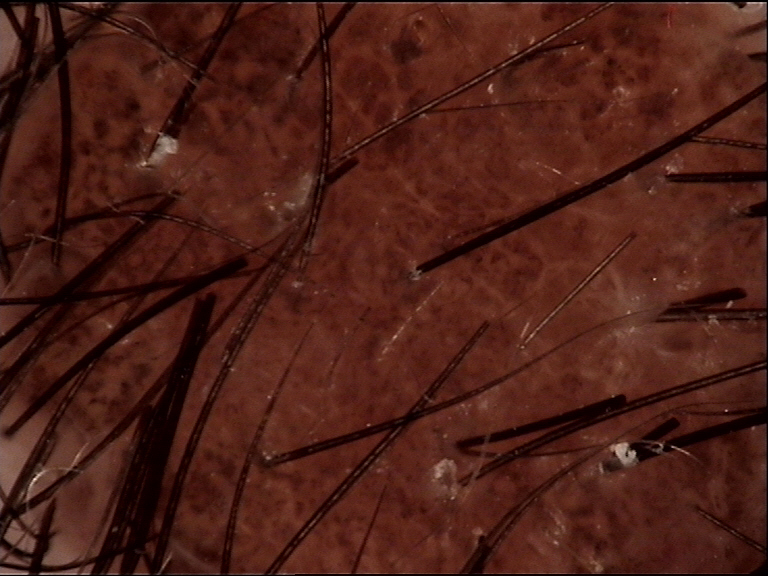Findings:
A skin lesion imaged with a dermatoscope. The architecture is that of a banal lesion.
Impression:
The diagnostic label was a dermal nevus.